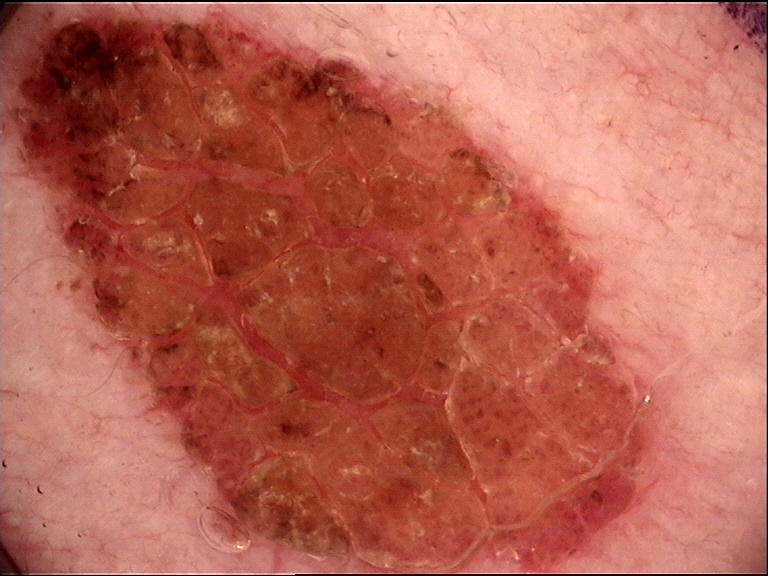Case: A dermatoscopic image of a skin lesion. Conclusion: Diagnosed as a dysplastic compound nevus.